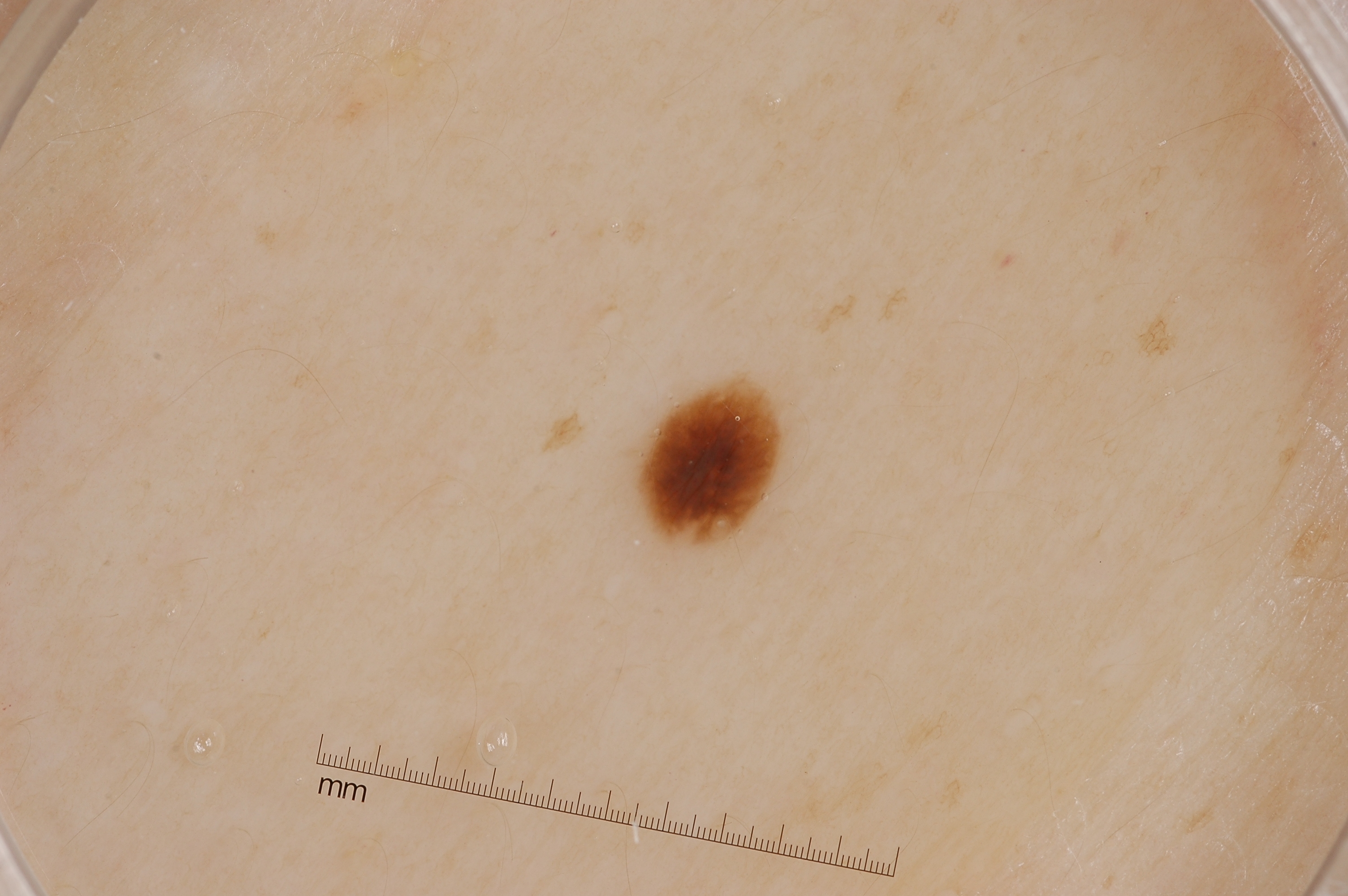Case summary:
A dermoscopic image of a skin lesion. A female subject, about 35 years old. With coordinates (x1, y1, x2, y2), the lesion is located at 643 385 779 546. A small lesion occupying a minor part of the field. Dermoscopic review identifies no streaks, pigment network, milia-like cysts, or negative network.
Assessment:
Consistent with a seborrheic keratosis, a benign lesion.